The patient considered this a rash; an image taken at a distance; texture is reported as raised or bumpy; reported duration is less than one week; the arm is involved; the lesion is associated with itching — 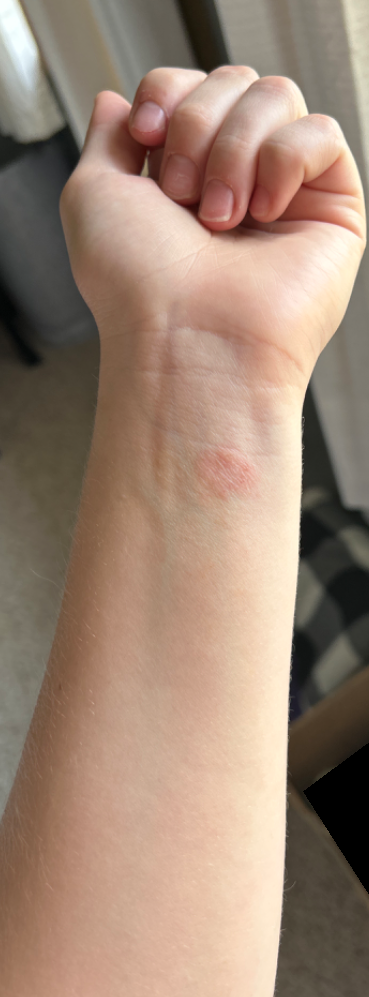Q: What was the assessment?
A: could not be assessed